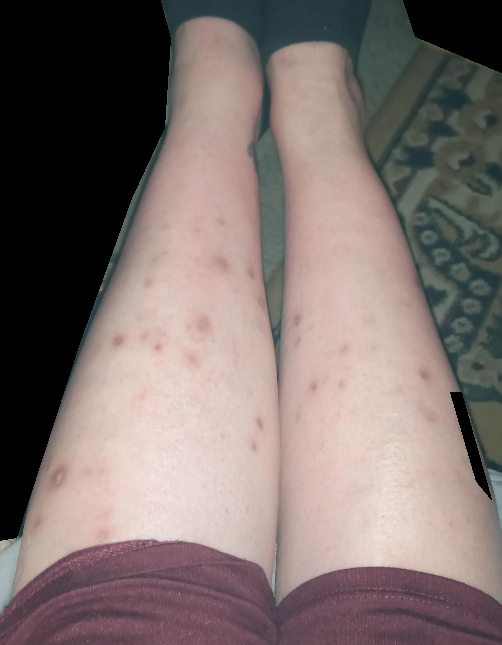The arm and leg are involved. The patient is female. The photo was captured at a distance. On teledermatology review, the leading impression is Prurigo nodularis; also raised was Folliculitis; possibly Insect Bite; a more distant consideration is Eczema; less likely is Vasculitis of the skin.